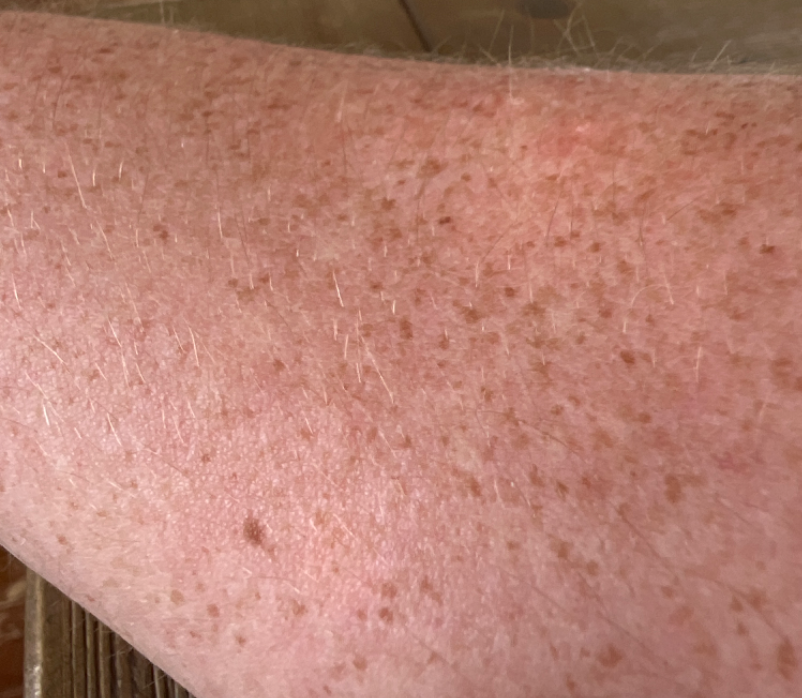Impression:
Eczema, Photodermatitis, Allergic Contact Dermatitis, Lentigo, Sunburn and Acquired poikiloderma were each considered, in no particular order.